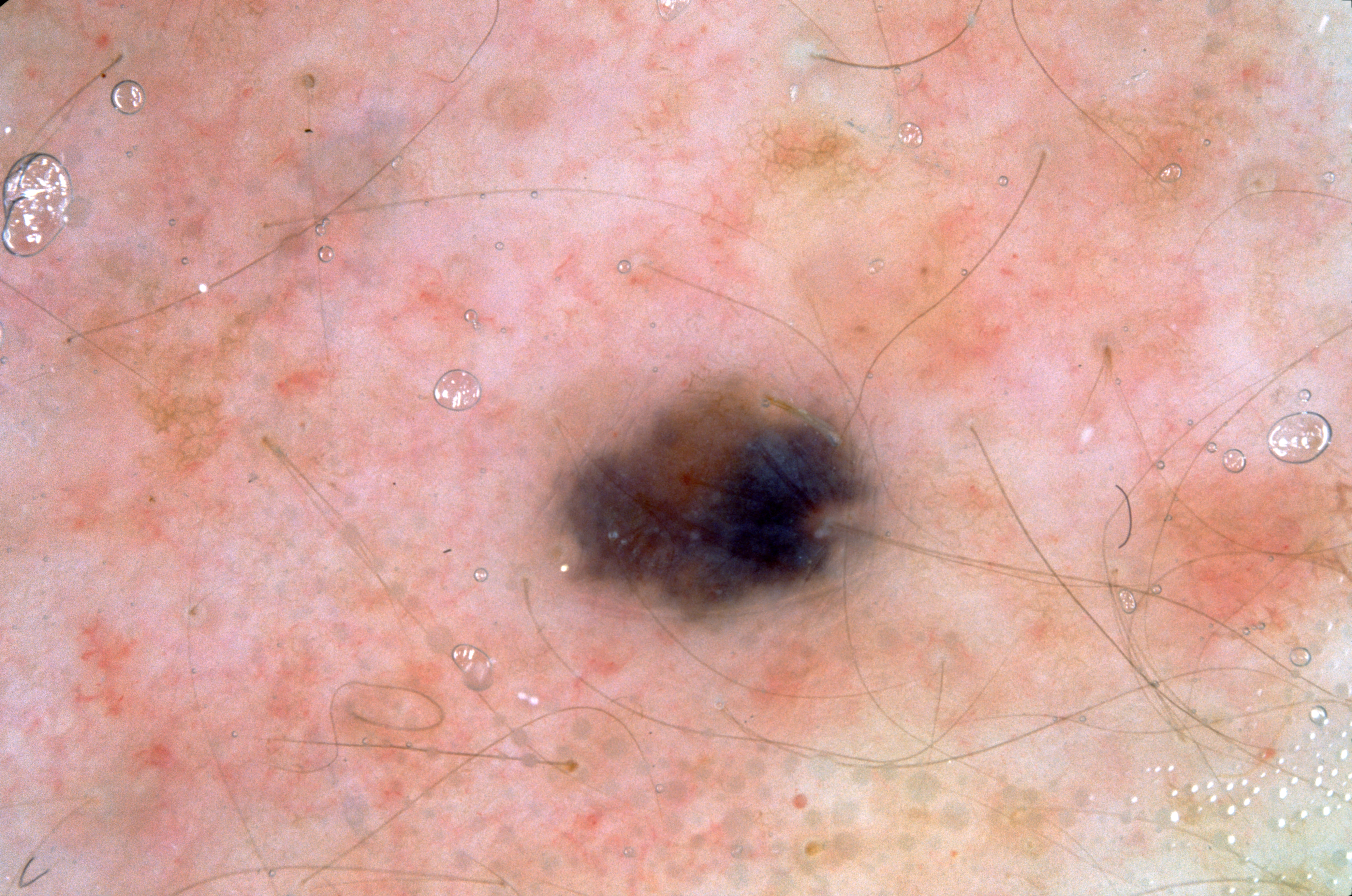A female patient aged approximately 45.
A dermatoscopic image of a skin lesion.
As (left, top, right, bottom), the lesion occupies the region [546,376,895,638].
A small lesion occupying a minor part of the field.
Dermoscopic examination shows no streaks, negative network, milia-like cysts, or pigment network.
The diagnostic assessment was a melanocytic nevus.